A dermoscopic view of a skin lesion — 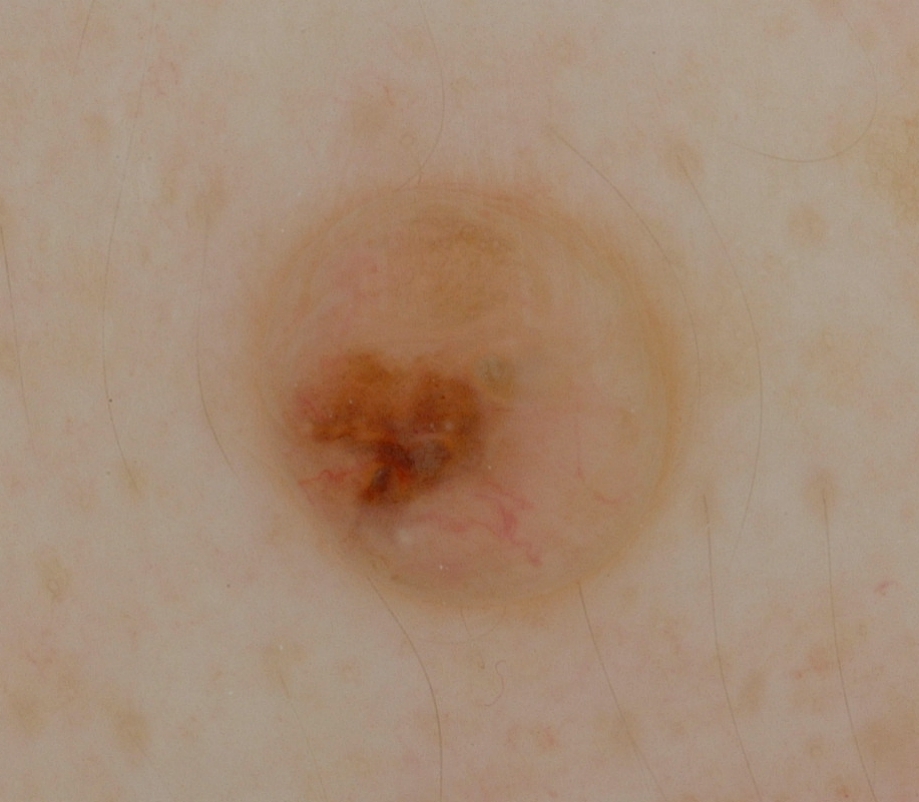* absent dermoscopic features — globules, streaks, pigment network, negative network, and milia-like cysts
* location — box(233, 173, 694, 622)
* impression — a melanocytic nevus